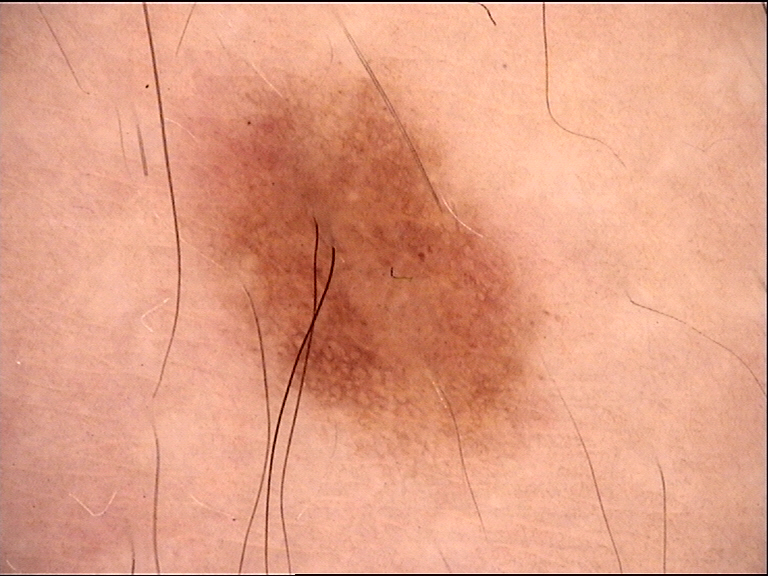A dermoscopic close-up of a skin lesion. This is a banal lesion. The diagnosis was a junctional nevus.